A skin lesion imaged with a dermatoscope.
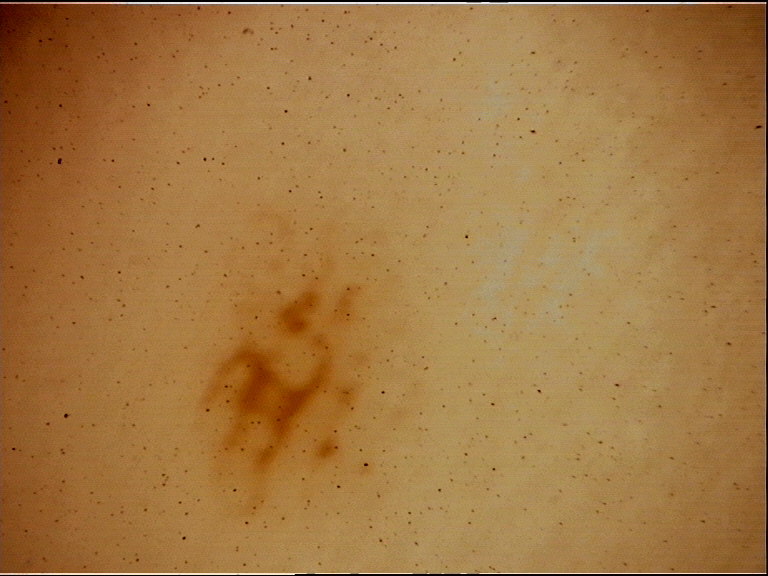Classified as an acral dysplastic junctional nevus.